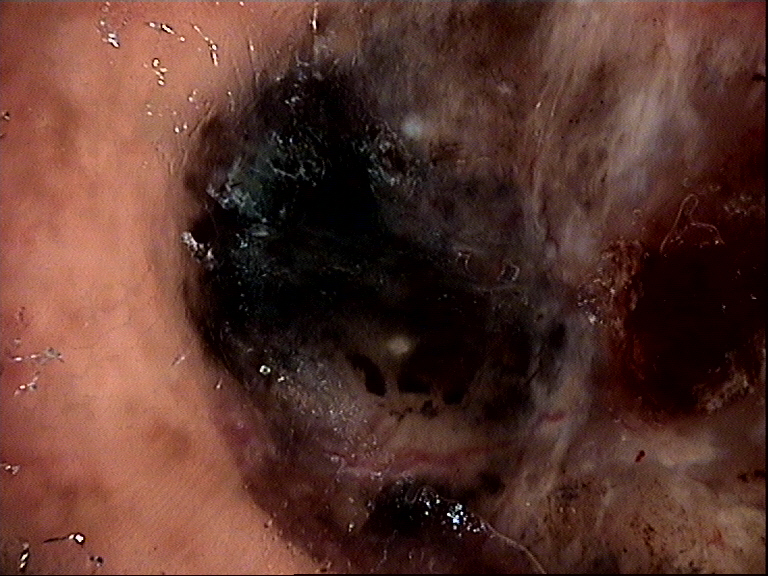<case>
  <image>dermoscopy</image>
  <diagnosis>
    <name>basal cell carcinoma</name>
    <code>bcc</code>
    <malignancy>malignant</malignancy>
    <super_class>non-melanocytic</super_class>
    <confirmation>histopathology</confirmation>
  </diagnosis>
</case>